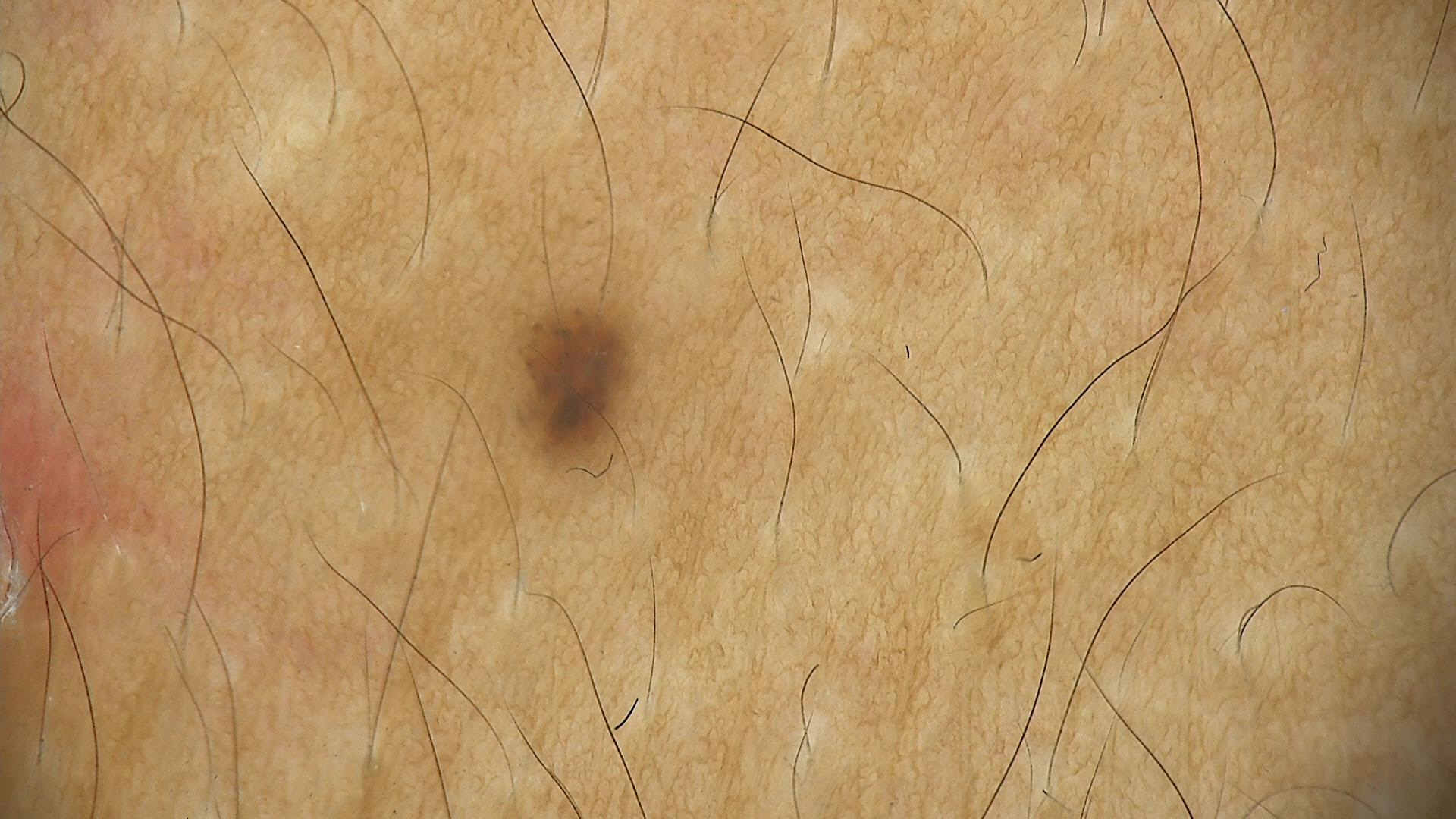Case:
• imaging — dermatoscopy
• diagnosis — dysplastic junctional nevus (expert consensus)